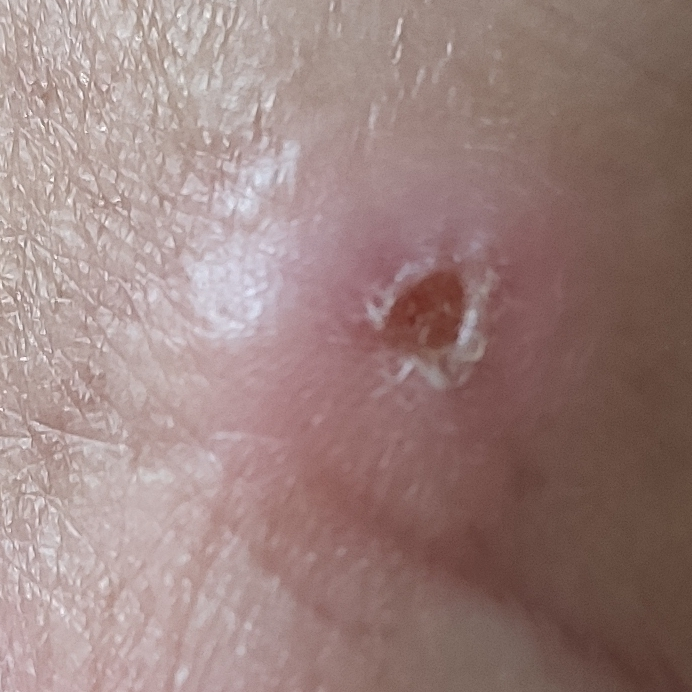Findings:
A female patient 57 years of age. The patient is Fitzpatrick phototype III. History notes pesticide exposure, alcohol use, and prior skin cancer (patient or family). The lesion is on a hand. The lesion measures 14 × 13 mm. The patient describes that the lesion has changed, hurts, is elevated, and has grown.
Conclusion:
Biopsy-confirmed as a skin cancer — a squamous cell carcinoma.